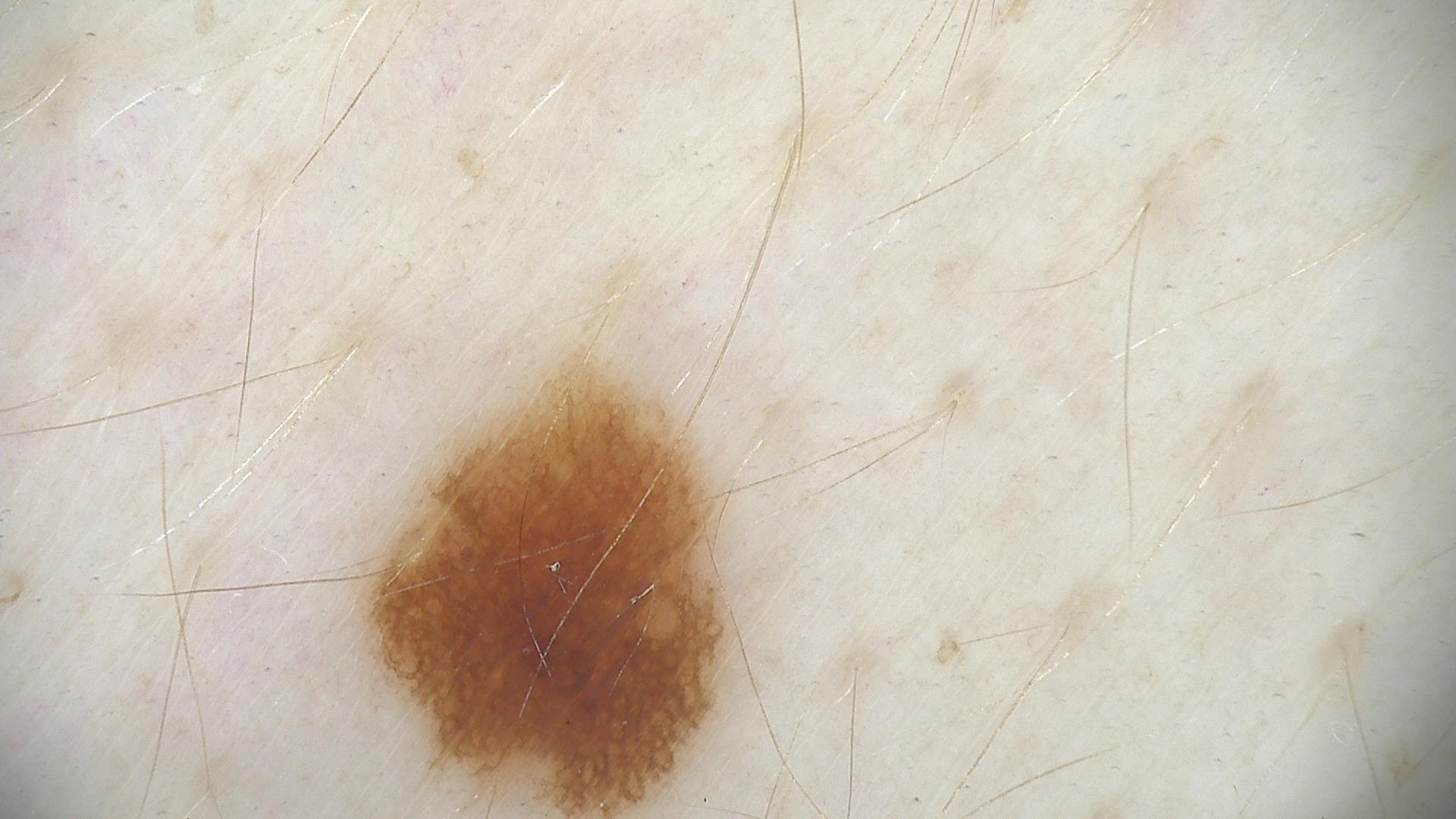{"diagnosis": {"name": "dysplastic junctional nevus", "code": "jd", "malignancy": "benign", "super_class": "melanocytic", "confirmation": "expert consensus"}}